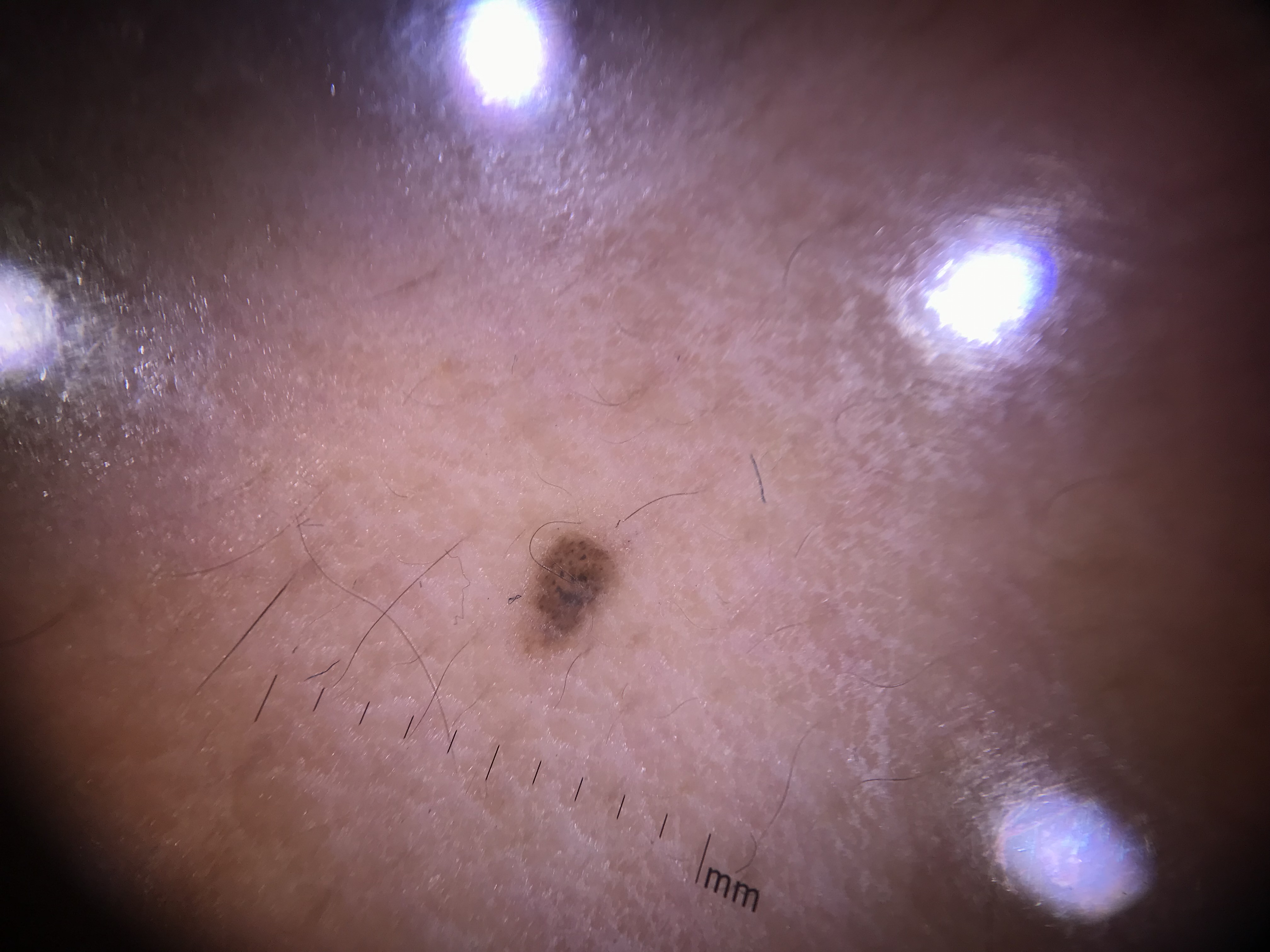Findings: The architecture is that of a banal lesion. Conclusion: Diagnosed as a junctional nevus.